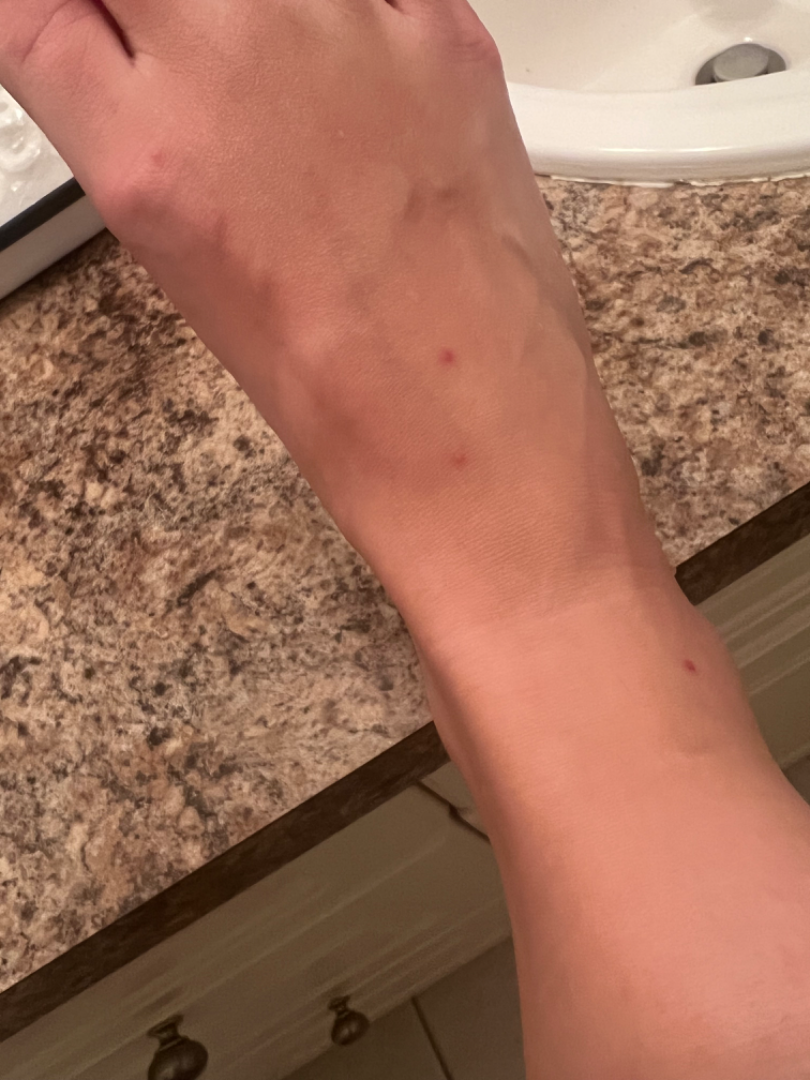Background: Texture is reported as fluid-filled and raised or bumpy. No associated lesion symptoms were reported. FST III. The patient indicates the condition has been present for about one day. An image taken at an angle. The affected area is the sole of the foot. Findings: Most consistent with Insect Bite; with consideration of Dermatofibroma; less likely is Skin cancer.